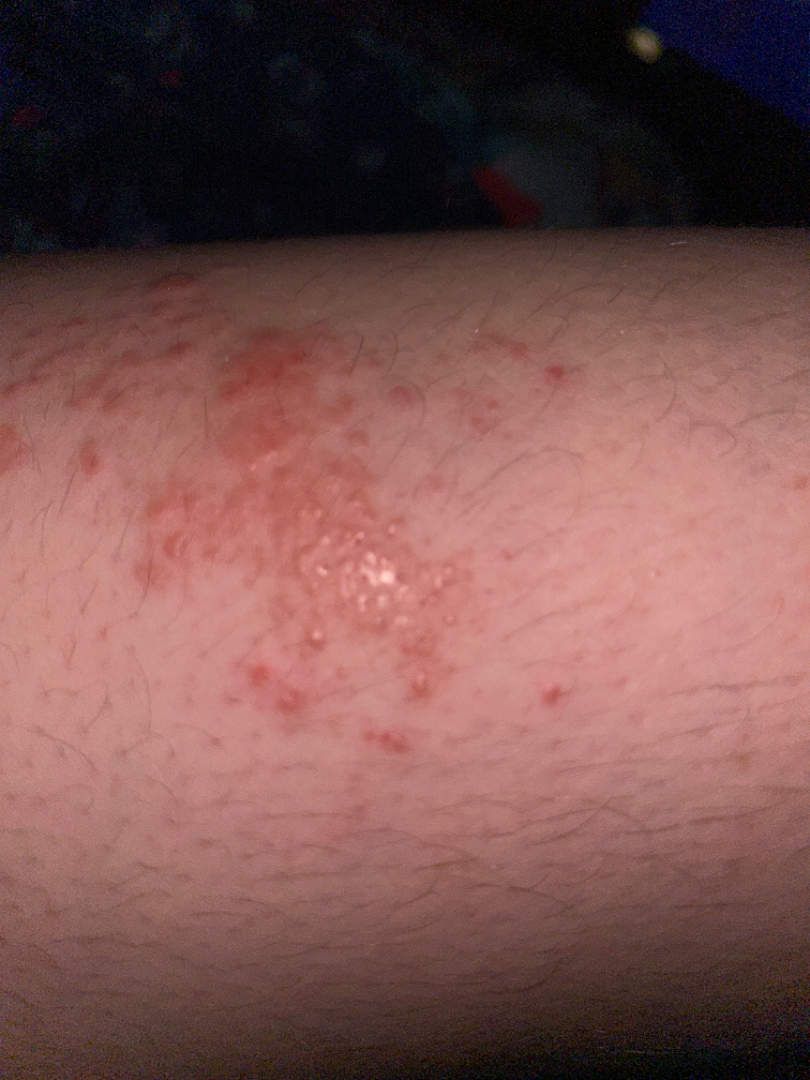Q: Any systemic symptoms?
A: none reported
Q: Texture?
A: raised or bumpy
Q: Duration?
A: one to four weeks
Q: Reported symptoms?
A: itching
Q: Where on the body?
A: leg
Q: Fitzpatrick or Monk tone?
A: Fitzpatrick skin type III; human graders estimated 2 on the Monk Skin Tone
Q: How does the patient describe it?
A: a rash
Q: How was the photo taken?
A: at an angle
Q: What is the differential diagnosis?
A: Allergic Contact Dermatitis (primary); Tinea (possible); Eczema (possible)